The photograph was taken at a distance; located on the front of the torso, back of the hand, arm, top or side of the foot and leg.
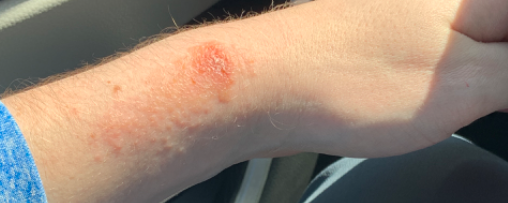texture = raised or bumpy, constitutional symptoms = none reported, duration = less than one week, patient's own categorization = a rash, lesion symptoms = itching, differential = reviewed remotely by one dermatologist: the reviewer's impression was Allergic Contact Dermatitis.